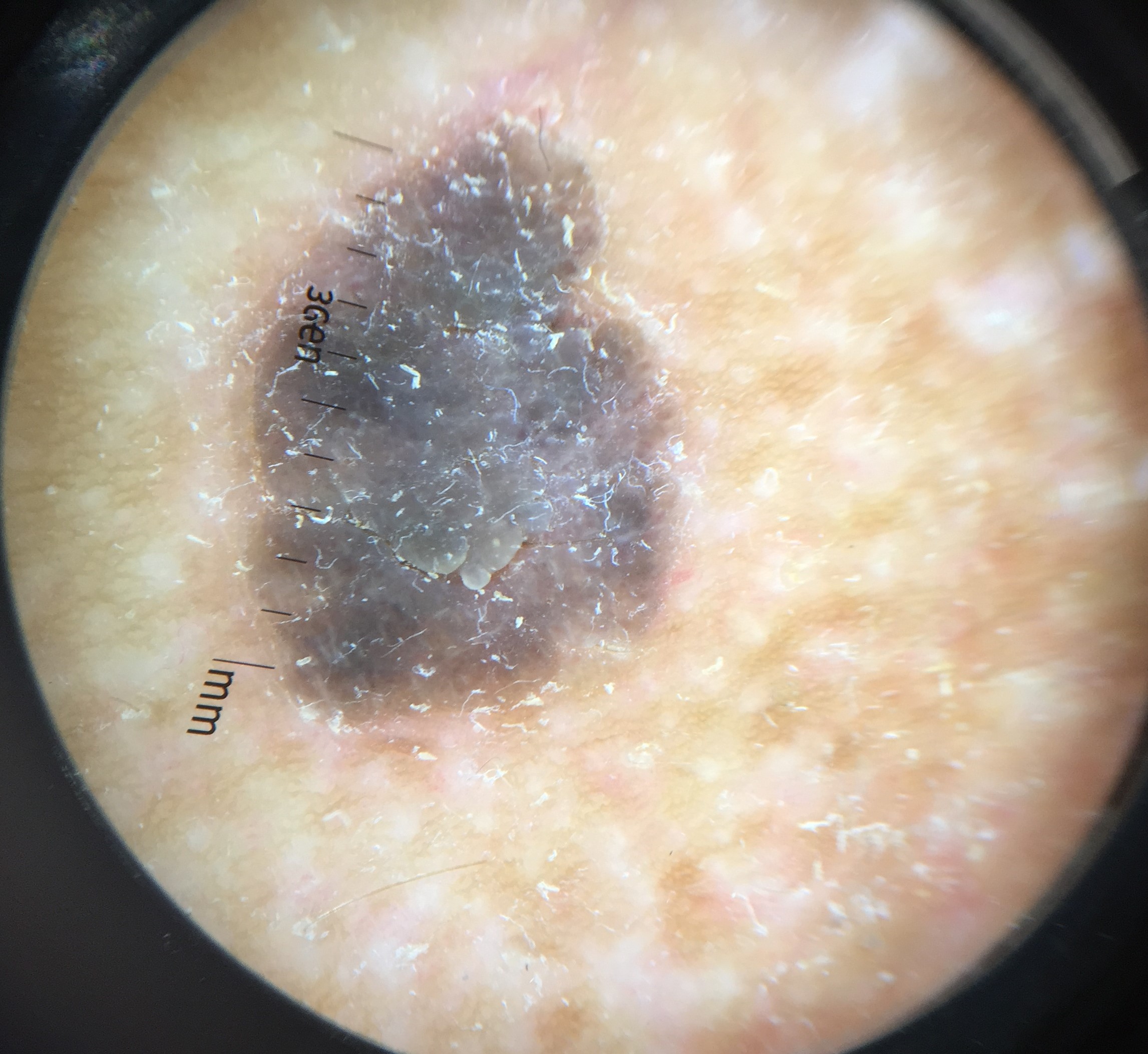Q: What is the diagnosis?
A: seborrheic keratosis (expert consensus)